A dermoscopic photograph of a skin lesion.
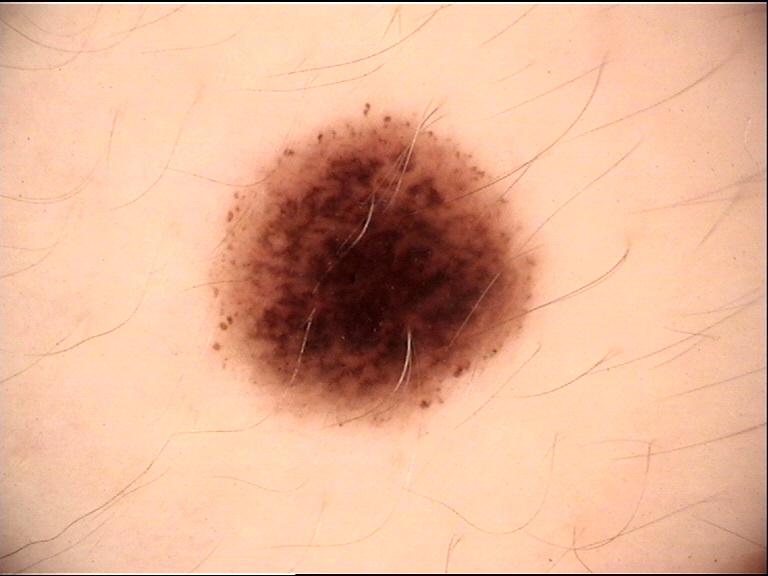Case:
– diagnosis — dysplastic compound nevus (expert consensus)